Reported lesion symptoms include itching · the photo was captured at an angle — 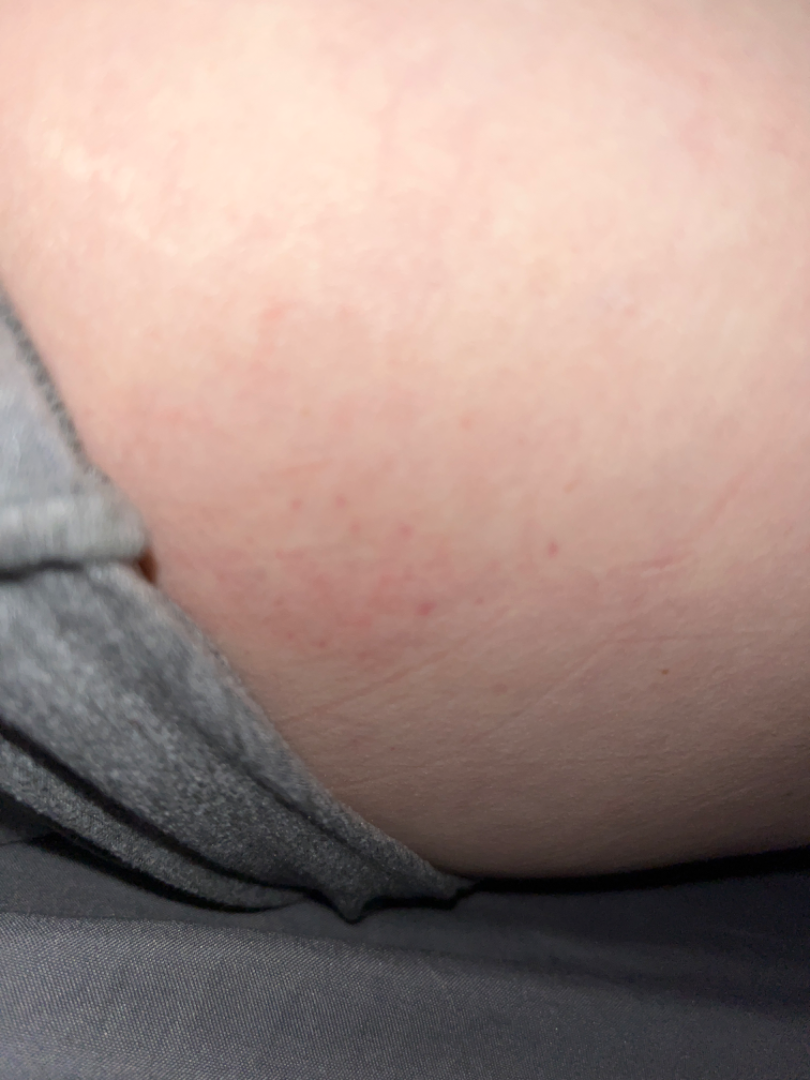On photographic review by a dermatologist, petechiae (primary); ecchymoses (possible).